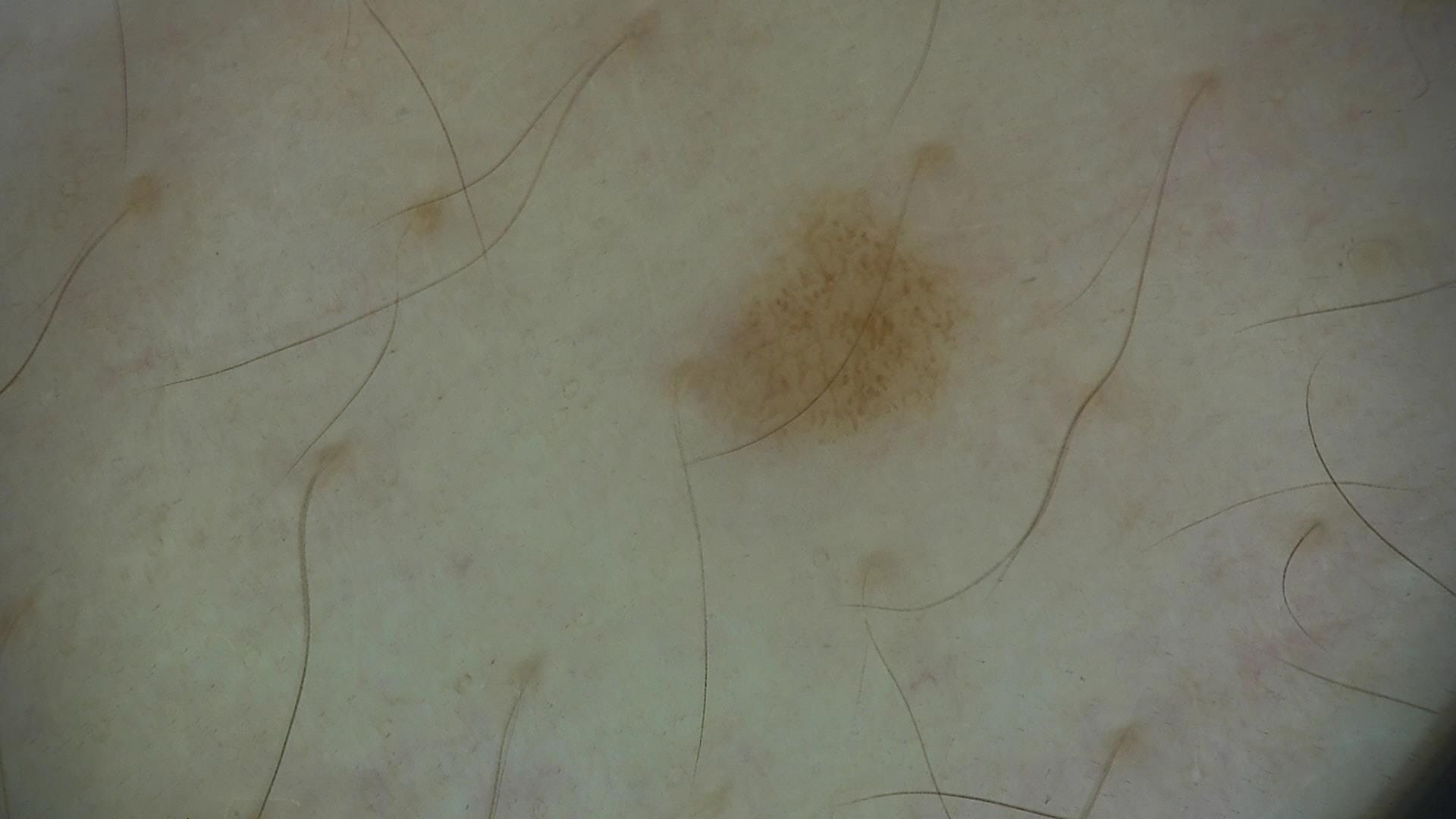Impression: Consistent with a benign lesion — a dysplastic junctional nevus.